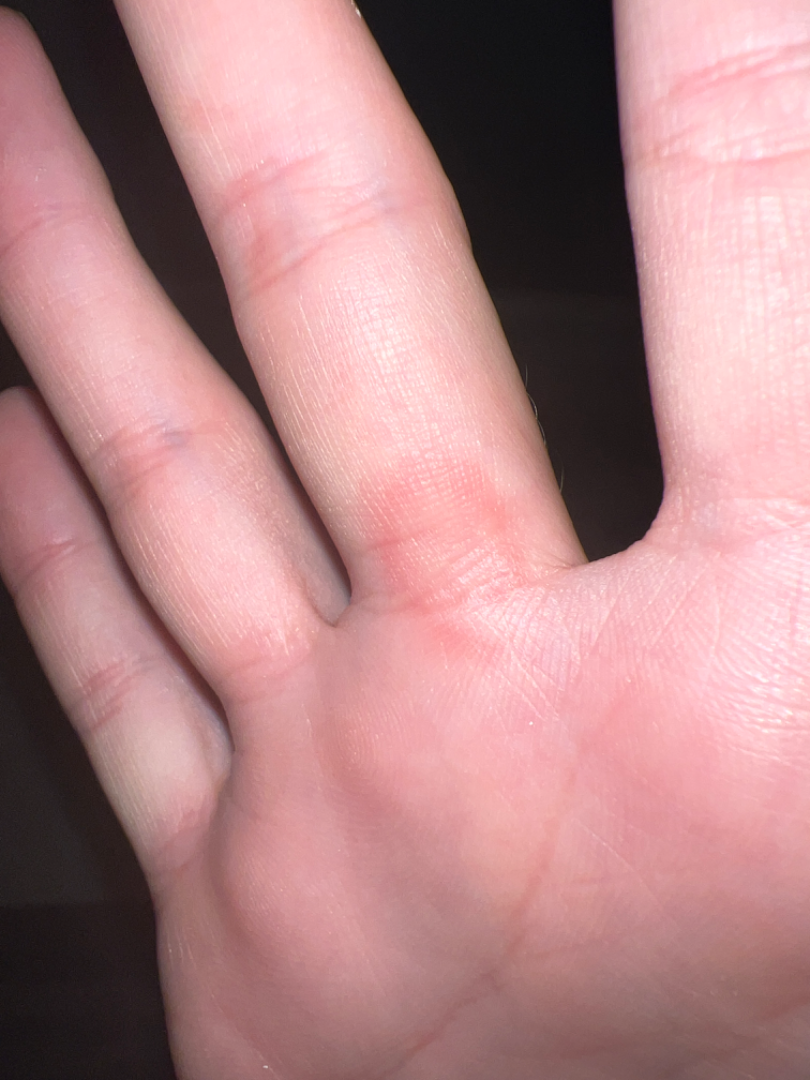Clinical context: The photograph is a close-up of the affected area. Skin tone: self-reported Fitzpatrick phototype II; non-clinician graders estimated MST 2. The patient notes the lesion is raised or bumpy. The patient described the issue as a rash. The subject is a female aged 18–29. The patient did not report lesion symptoms. Located on the palm. No associated systemic symptoms reported. Assessment: One reviewing dermatologist: Viral Exanthem, Erythema multiforme and Drug Rash were each considered, in no particular order.